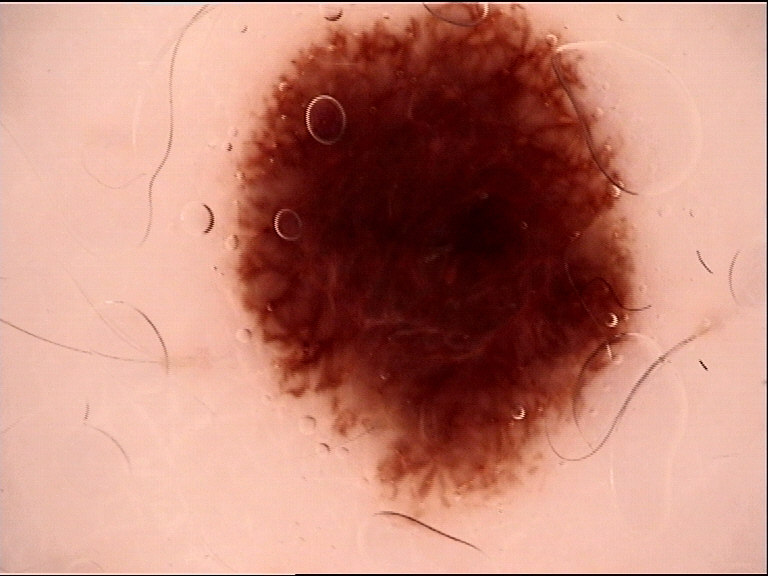A skin lesion imaged with a dermatoscope. Labeled as a dysplastic junctional nevus.